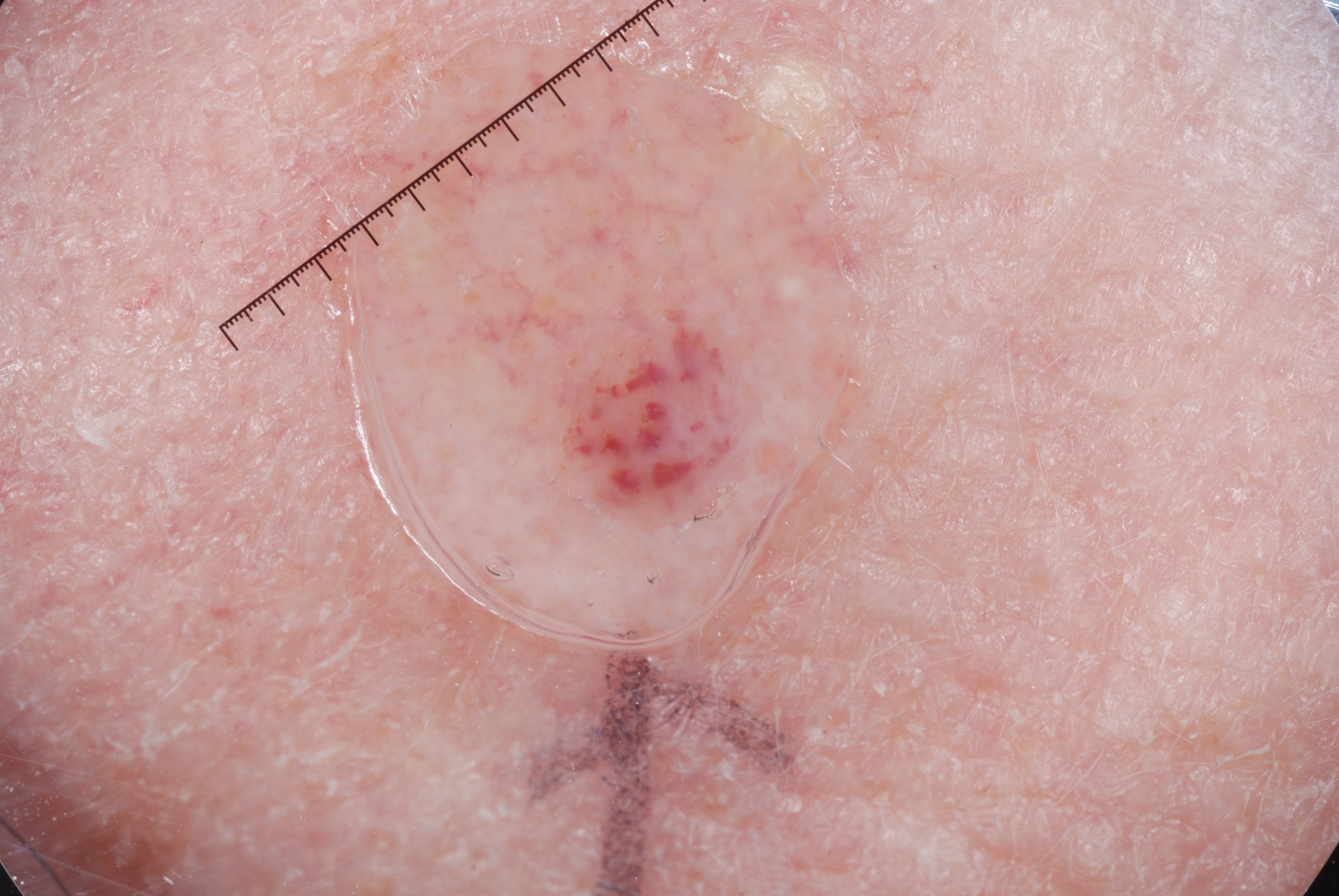Case summary:
A dermoscopic image of a skin lesion. A male subject roughly 70 years of age. The lesion covers approximately 4% of the dermoscopic field. As (left, top, right, bottom), the lesion spans 534/299/778/546. Dermoscopic assessment notes milia-like cysts.
Assessment:
Consistent with a melanocytic nevus, a benign skin lesion.